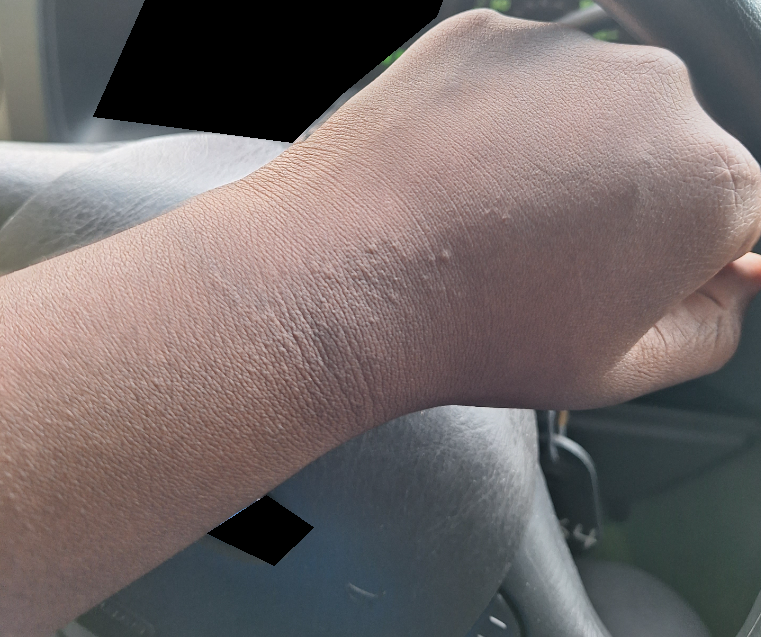differential: Chronic dermatitis, NOS